The contributor reports the lesion is raised or bumpy and rough or flaky · the contributor reports the condition has been present for more than one year · the subject is 60–69, male · the lesion involves the back of the hand · the photo was captured at an angle · skin tone: Fitzpatrick skin type II · the patient also reports fatigue and joint pain:
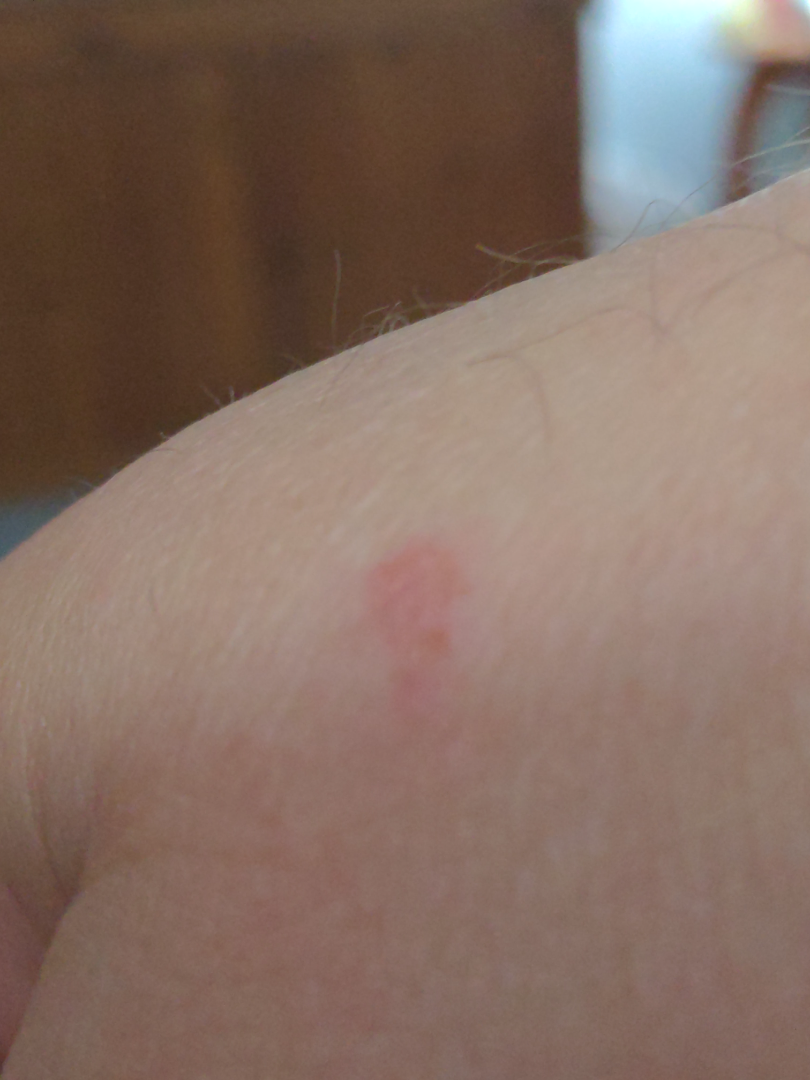Q: What is the dermatologist's impression?
A: the impression was split between Eczema, Insect Bite and Herpes Simplex